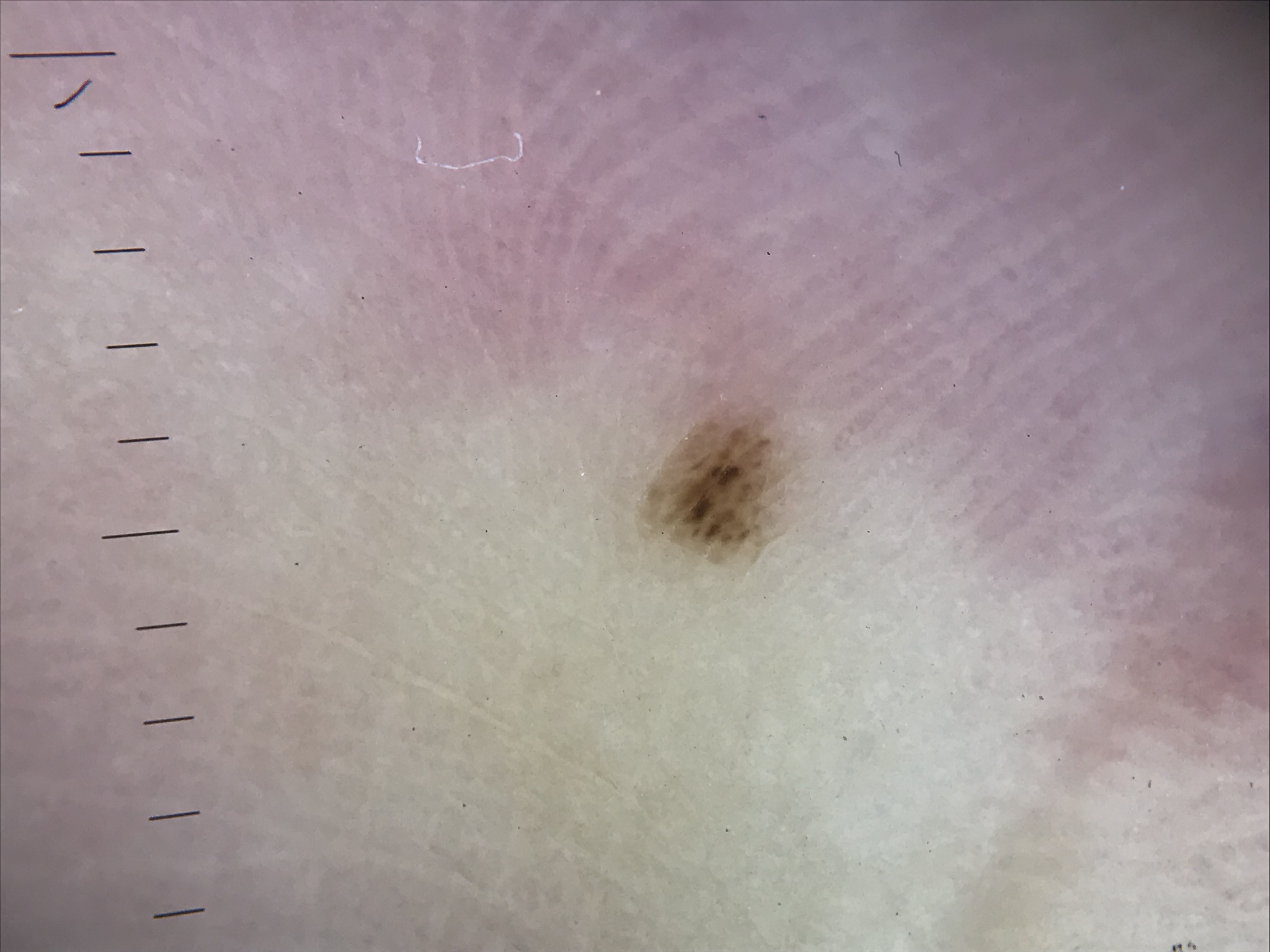diagnosis — acral junctional nevus (expert consensus).